The patient is a female aged 18–29 · the lesion involves the arm, head or neck and leg · skin tone: Fitzpatrick III; lay reviewers estimated Monk Skin Tone 2 or 3 · the patient notes the condition has been present for about one day · texture is reported as raised or bumpy · this image was taken at a distance · the patient considered this a rash · symptoms reported: enlargement, itching and bothersome appearance:
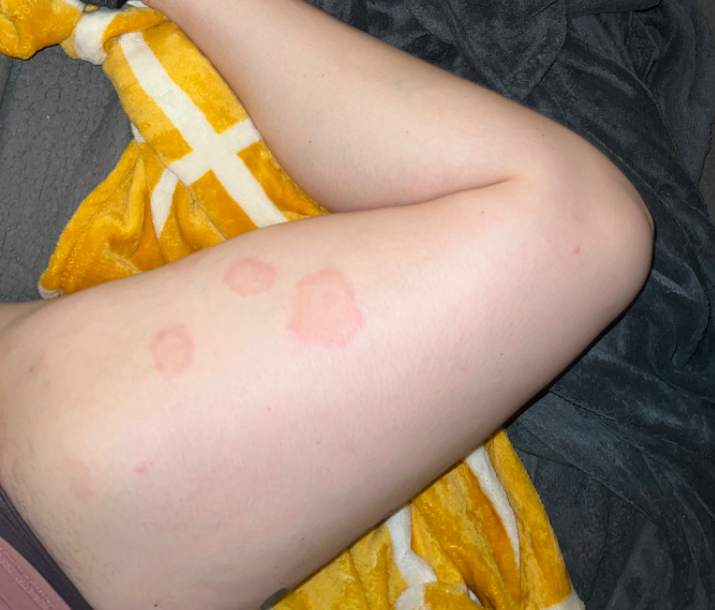{
  "differential": [
    "Drug Rash",
    "Leukocytoclastic Vasculitis",
    "Erythema multiforme"
  ]
}